By self-report, a personal history of skin cancer, no family history of skin cancer, and no sunbed use · a moderate number of moles by the patient's own estimate — 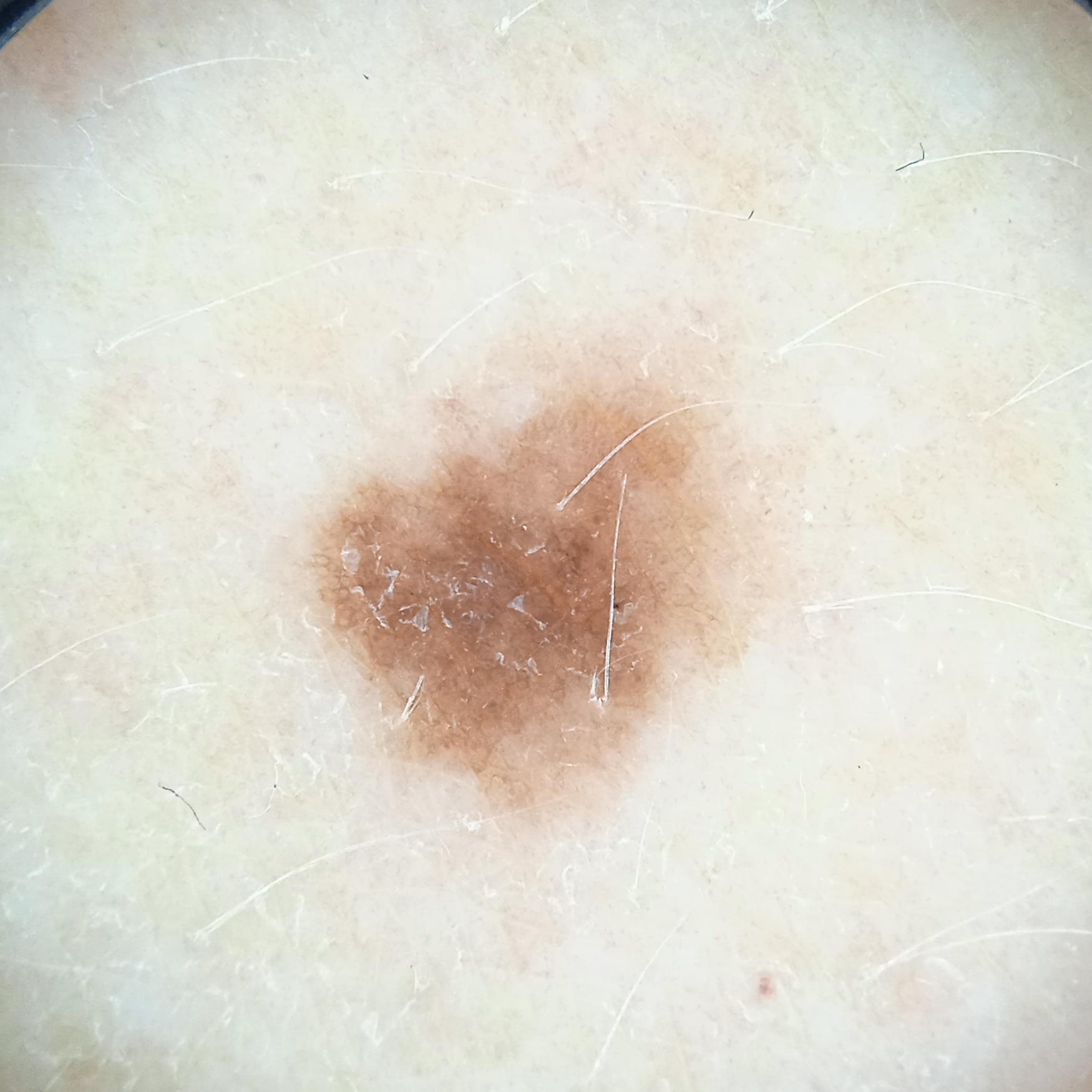Q: Where is the lesion?
A: the torso
Q: How large is the lesion?
A: 5.4 mm
Q: What was the diagnosis?
A: melanocytic nevus (dermatologist consensus)